Located on the leg · the subject is 18–29, female · an image taken at an angle:
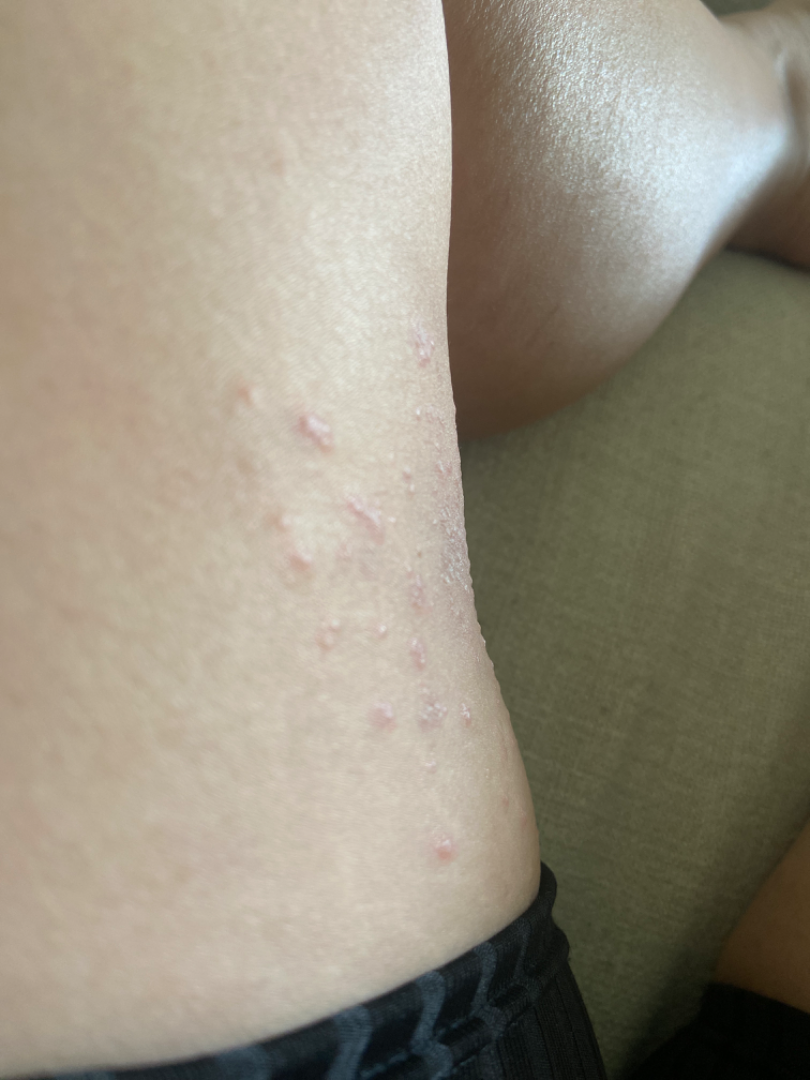lesion texture: rough or flaky and raised or bumpy
constitutional symptoms: none reported
lesion symptoms: enlargement, itching, burning and darkening
skin tone: Fitzpatrick skin type II; lay reviewers estimated a Monk Skin Tone of 2
symptom duration: one to four weeks
diagnostic considerations: Psoriasis (possible); Lichen planus/lichenoid eruption (possible); Eczema (possible); Insect Bite (lower probability); Allergic Contact Dermatitis (lower probability)